Close-up view; female contributor, age 40–49; the affected area is the top or side of the foot — 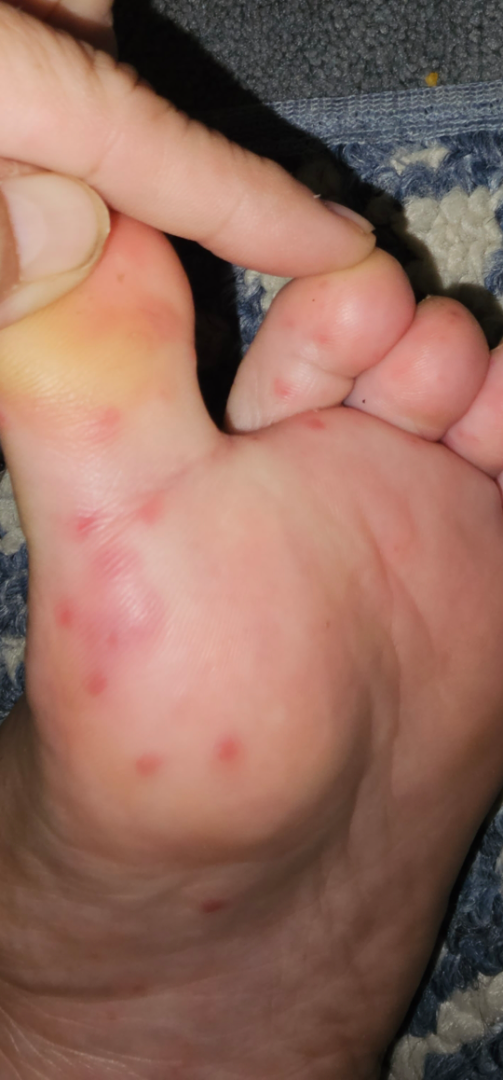On remote dermatologist review, Hand foot and mouth disease (most likely); Syphilis (possible); Rocky Mountain spotted fever (possible).